The lesion involves the top or side of the foot, arm, leg and back of the hand; the photograph is a close-up of the affected area — 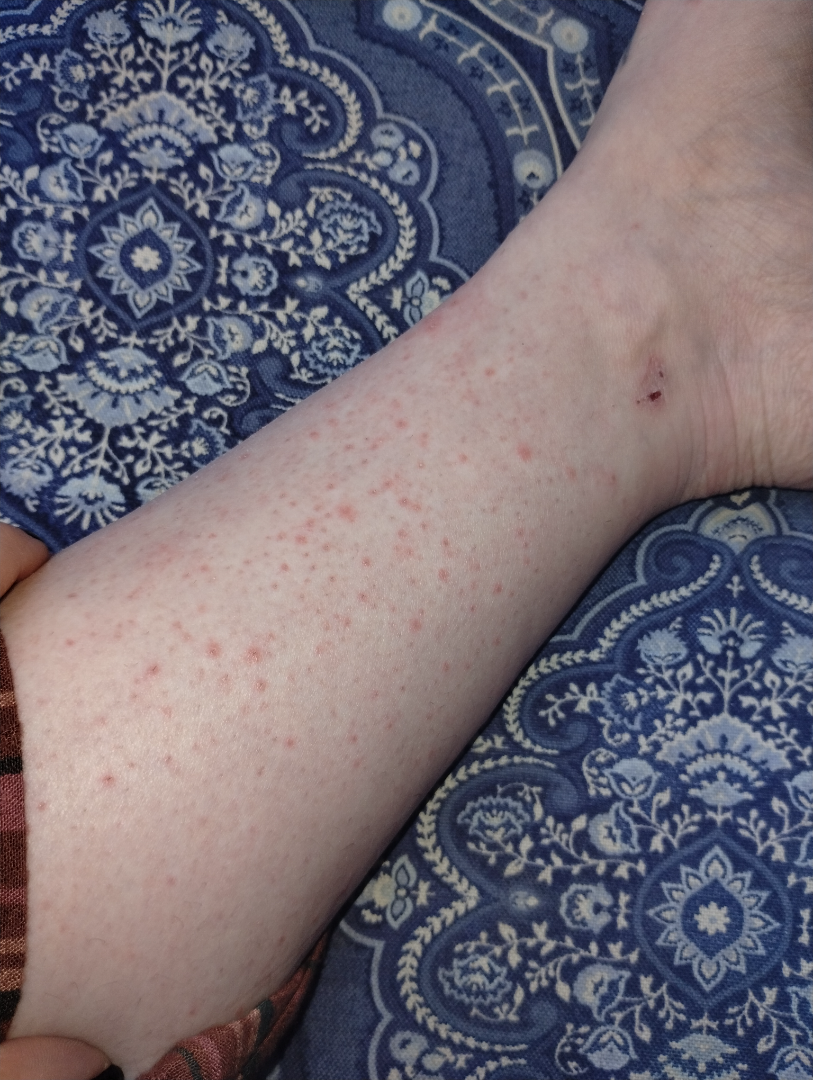Q: How long has this been present?
A: less than one week
Q: What is the lesion texture?
A: raised or bumpy and rough or flaky
Q: What symptoms does the patient report?
A: itching
Q: What is the differential diagnosis?
A: Folliculitis (considered); Vasculitis of the skin (considered)